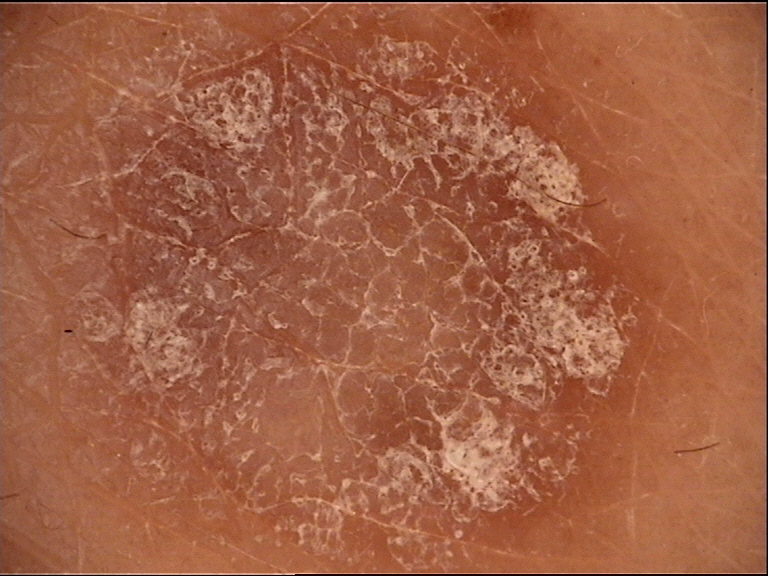– diagnostic label · dermatofibroma (expert consensus)